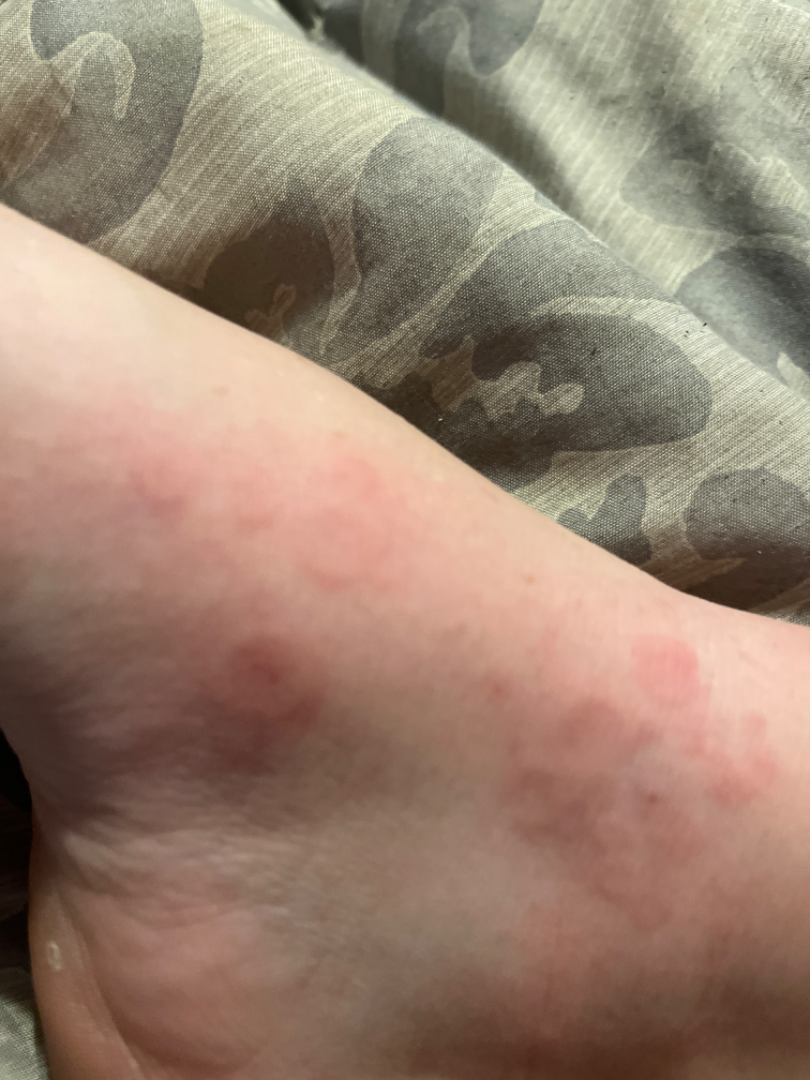assessment: ungradable on photographic review
texture: raised or bumpy
shot_type: close-up
patient_category: a rash
duration: less than one week
symptoms:
  - itching
  - burning
  - bothersome appearance
body_site: top or side of the foot
skin_tone:
  fitzpatrick: II
  monk_skin_tone:
    - 2
    - 3